A skin lesion imaged with a dermatoscope: 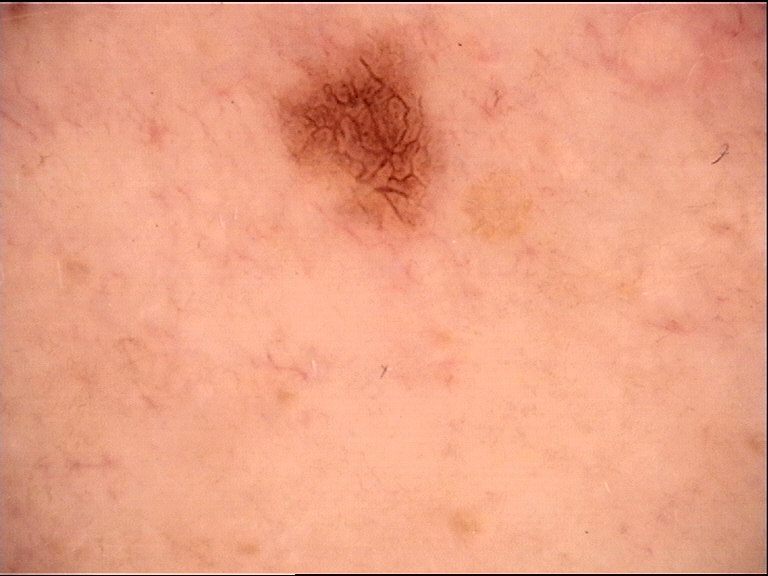Impression: Labeled as a dysplastic junctional nevus.